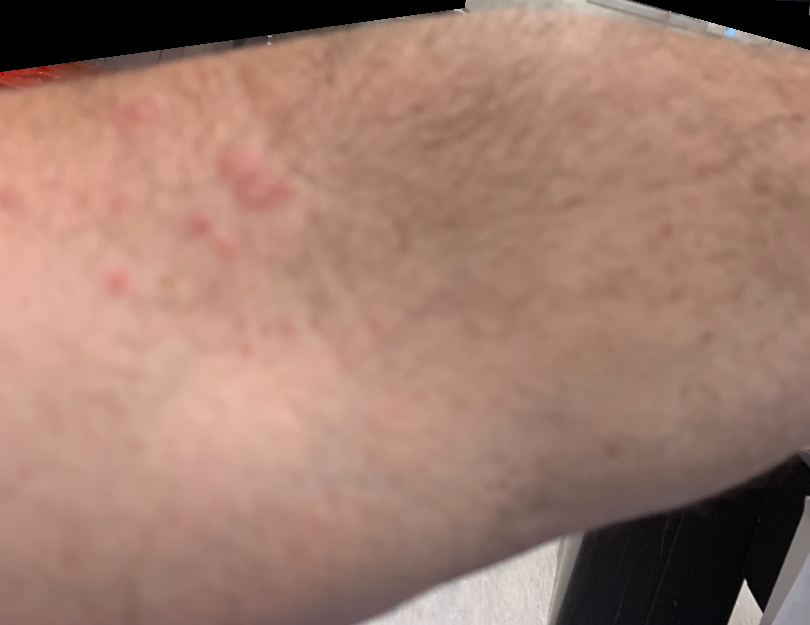Impression: On remote dermatologist review, Herpes Zoster (weight 0.50); Allergic Contact Dermatitis (weight 0.50).